A female patient age 51 · a clinical photograph showing a skin lesion:
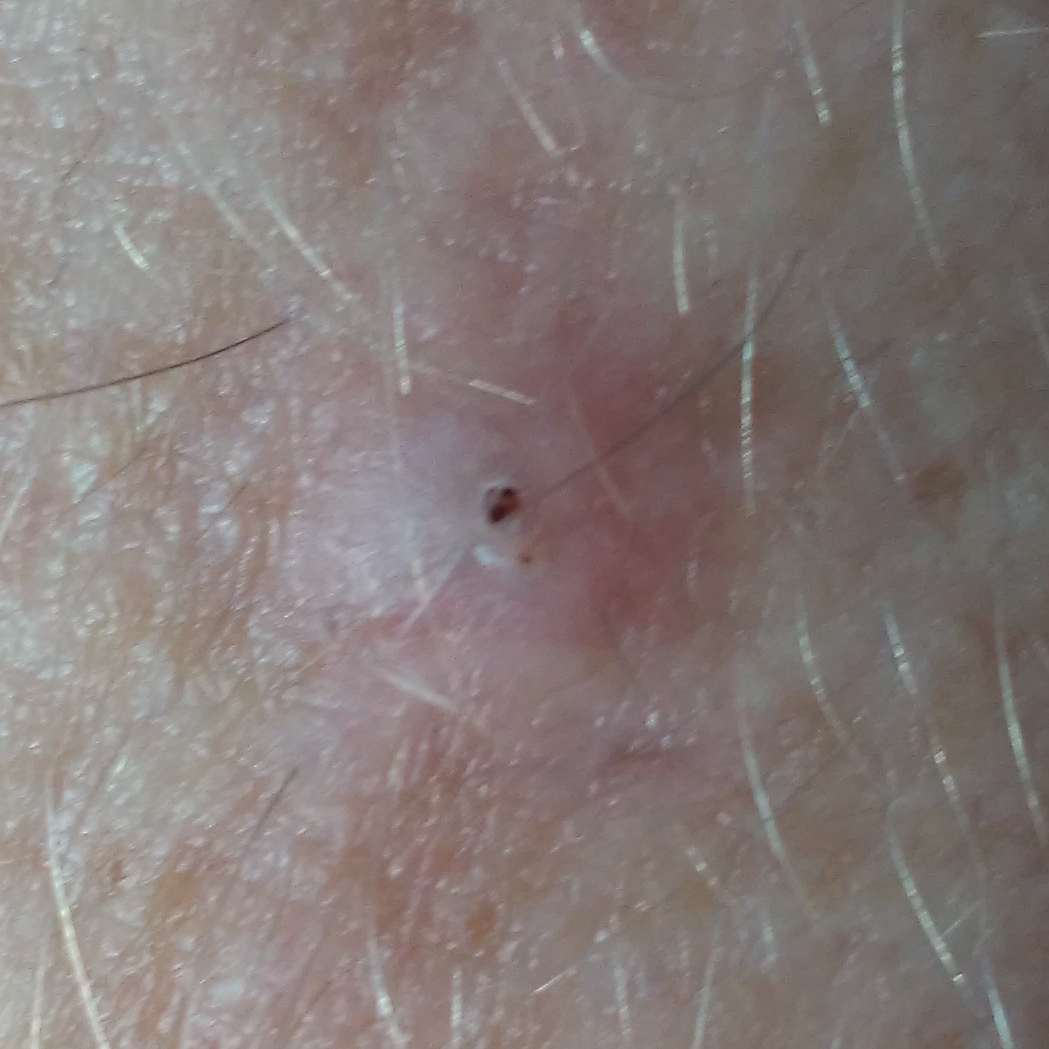body site: a forearm | symptoms: itching, elevation | diagnosis: actinic keratosis (biopsy-proven).